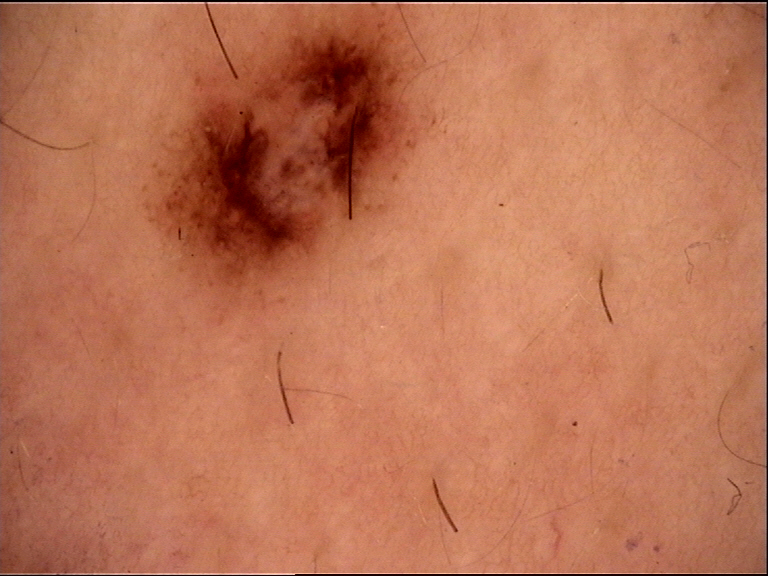class: dysplastic compound nevus (expert consensus)